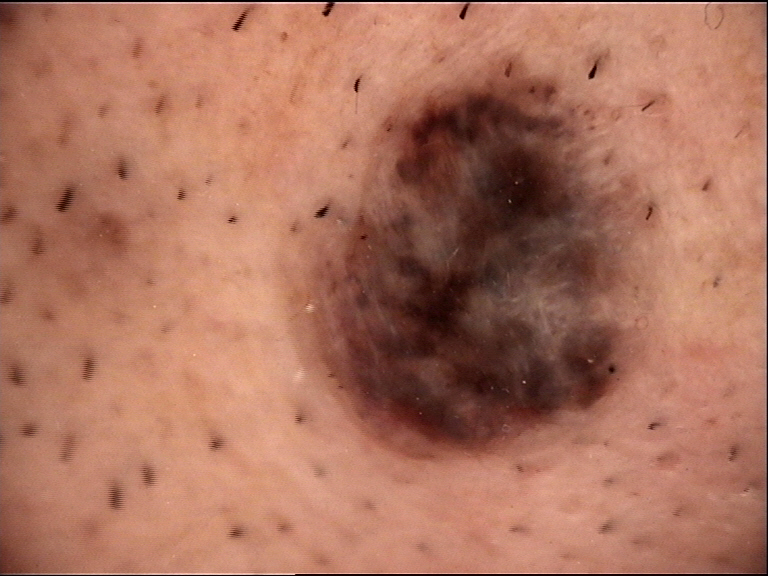Consistent with a benign lesion — a congenital dysplastic compound nevus.